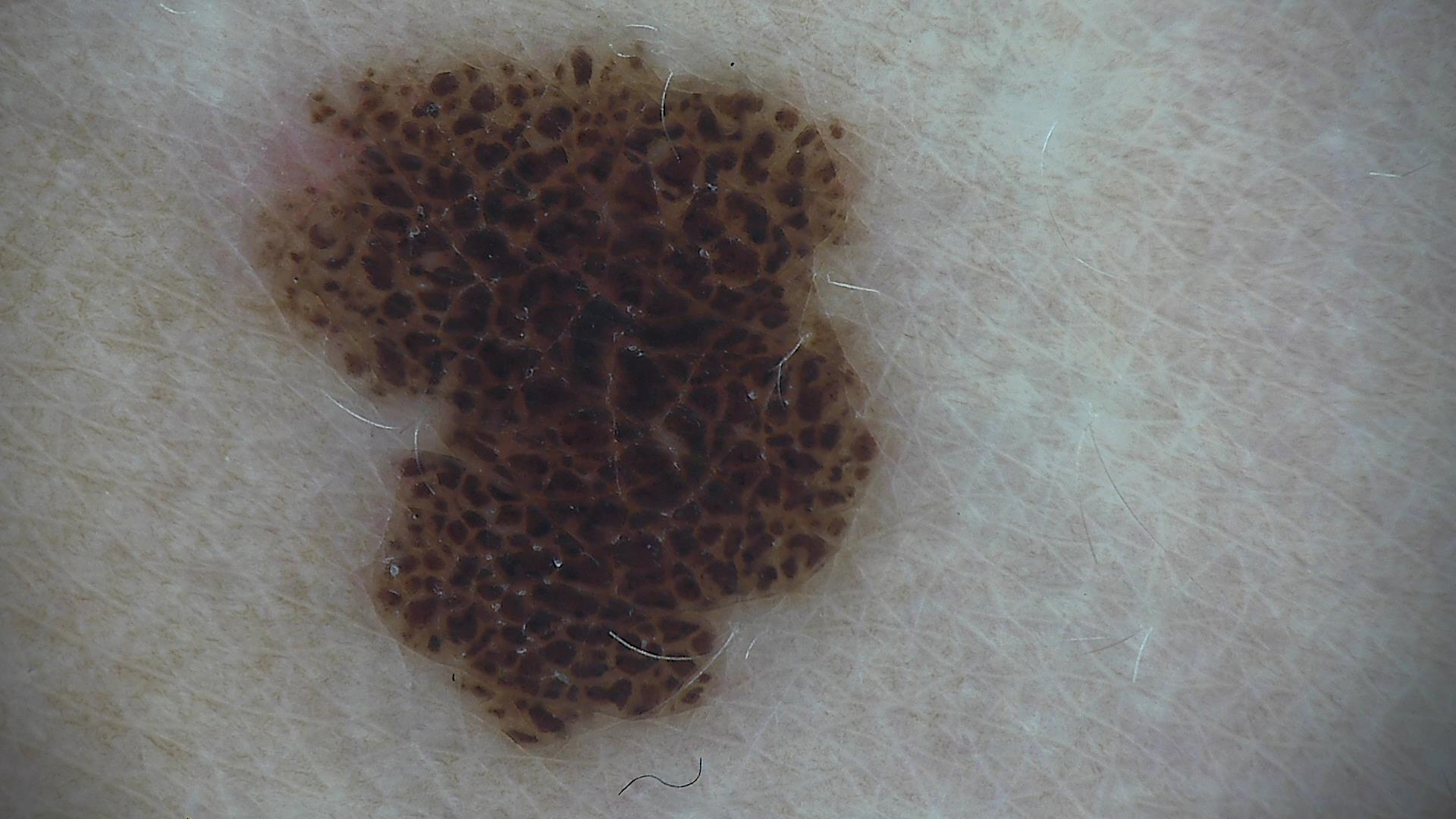A dermatoscopic image of a skin lesion.
Classified as a benign lesion — a dysplastic compound nevus.